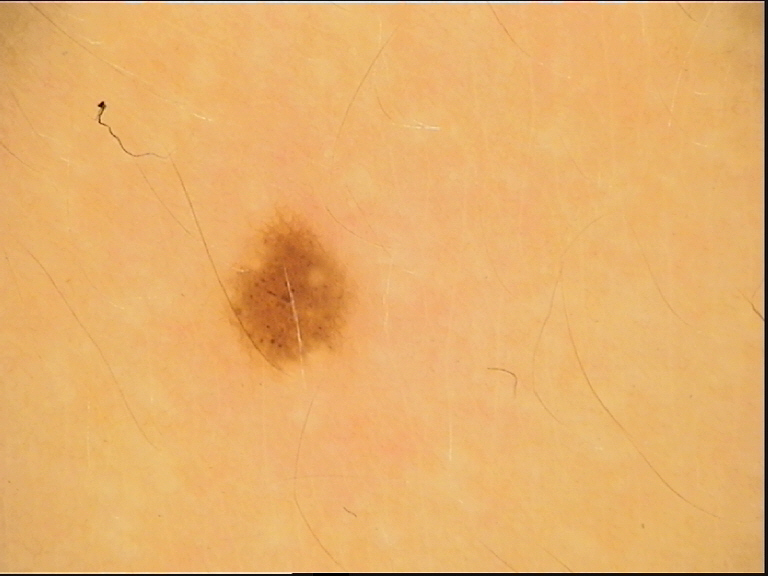diagnostic label — dysplastic junctional nevus (expert consensus).